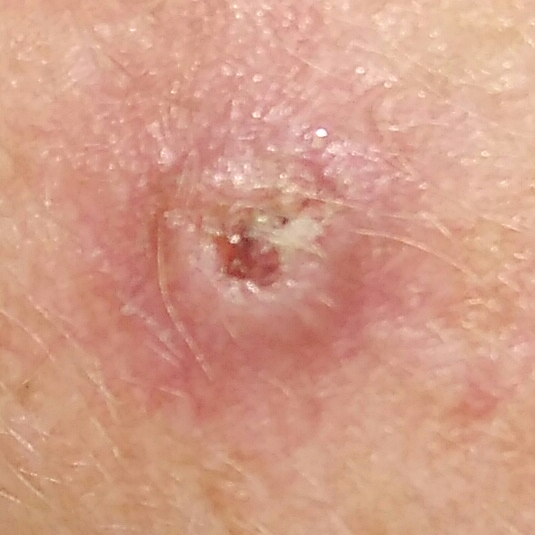Q: What is this lesion?
A: squamous cell carcinoma (biopsy-proven)